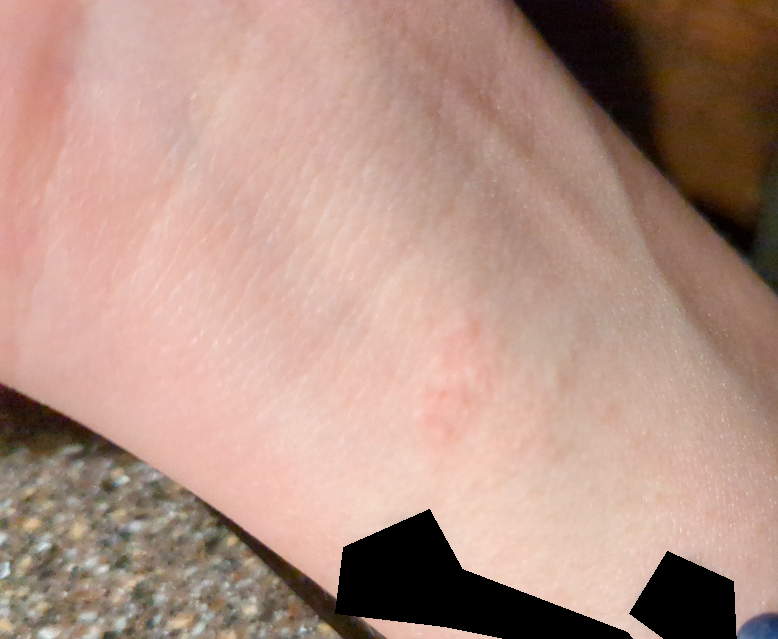<summary>
  <duration>one to four weeks</duration>
  <texture>fluid-filled, rough or flaky, raised or bumpy</texture>
  <shot_type>at an angle</shot_type>
  <body_site>leg, arm</body_site>
  <symptoms>itching, enlargement</symptoms>
  <systemic_symptoms>fatigue</systemic_symptoms>
  <patient_category>a rash</patient_category>
  <patient>female, age 18–29</patient>
  <differential>
    <leading>Allergic Contact Dermatitis</leading>
    <considered>Contact dermatitis</considered>
    <unlikely>Eczema, Irritant Contact Dermatitis, Herpes Simplex</unlikely>
  </differential>
</summary>